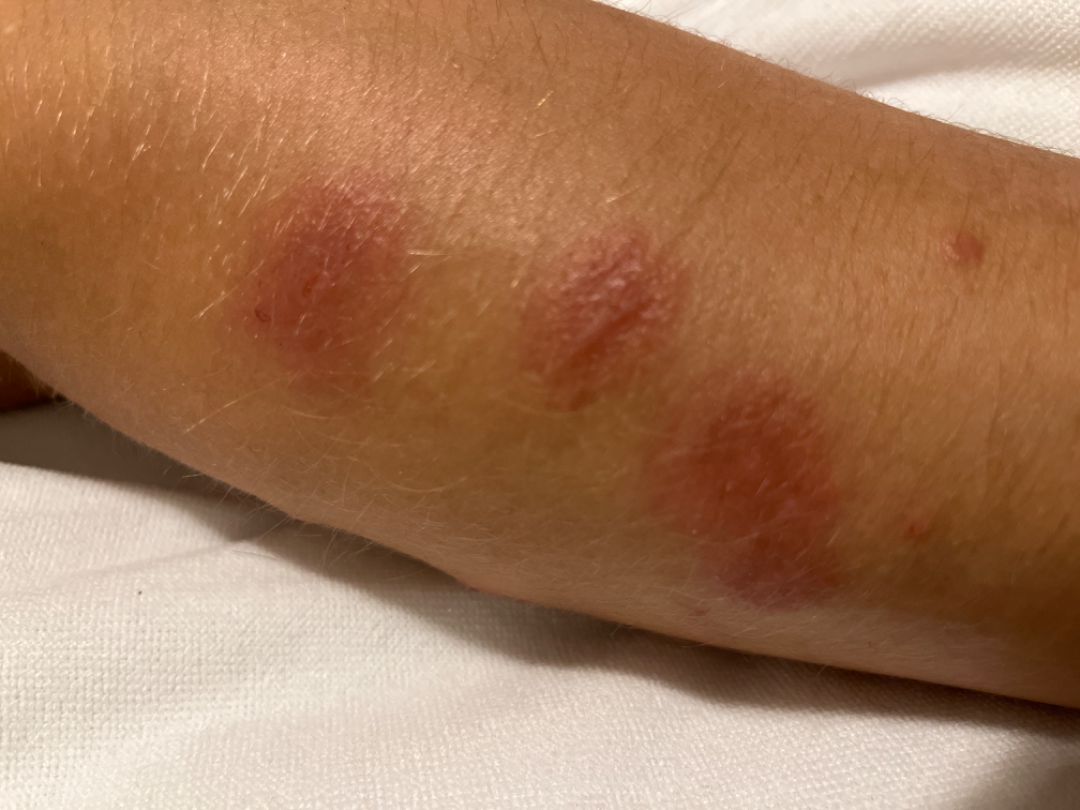Assessment:
The reviewer was unable to grade this case for skin condition.
Clinical context:
The patient indicates itching and enlargement. The arm is involved. The photo was captured at an angle. Female subject, age 18–29. The patient reported no systemic symptoms. The patient indicates the condition has been present for one to four weeks. Self-categorized by the patient as a rash. The patient indicates the lesion is raised or bumpy and fluid-filled.